The patient is a female aged 18–29. The leg is involved. An image taken at an angle — 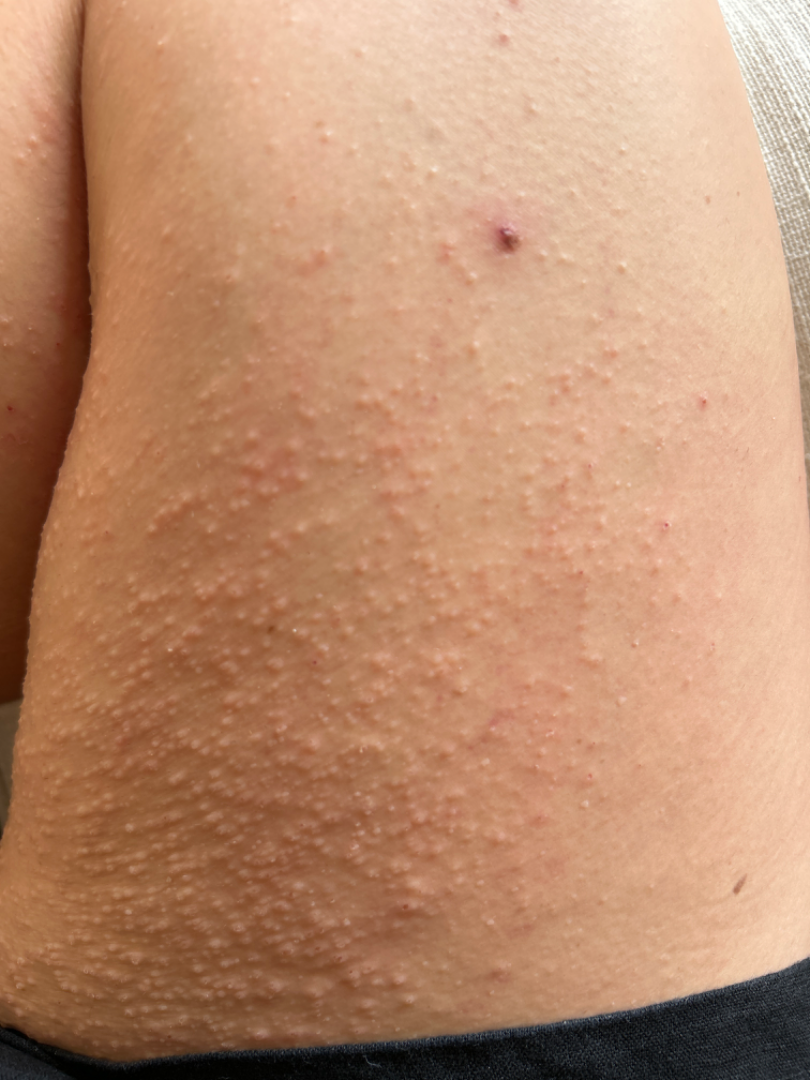{
  "assessment": "not assessable",
  "skin_tone": {
    "fitzpatrick": "III",
    "fitzpatrick_source": "self_reported"
  },
  "systemic_symptoms": "none reported",
  "patient_category": "a rash",
  "duration": "one to four weeks"
}